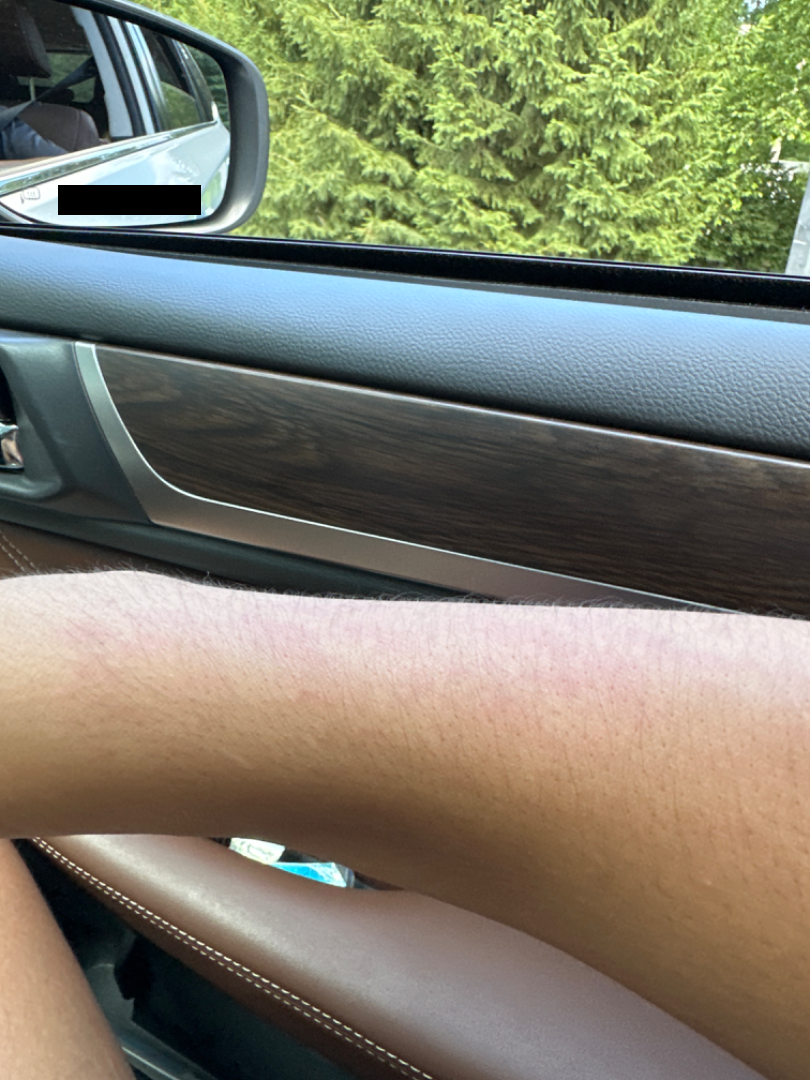| feature | finding |
|---|---|
| assessment | indeterminate |